Female subject, age 40–49 · the lesion is associated with itching · the lesion involves the head or neck · the patient considered this a rash · the lesion is described as raised or bumpy · the condition has been present for one to four weeks · the photograph is a close-up of the affected area — 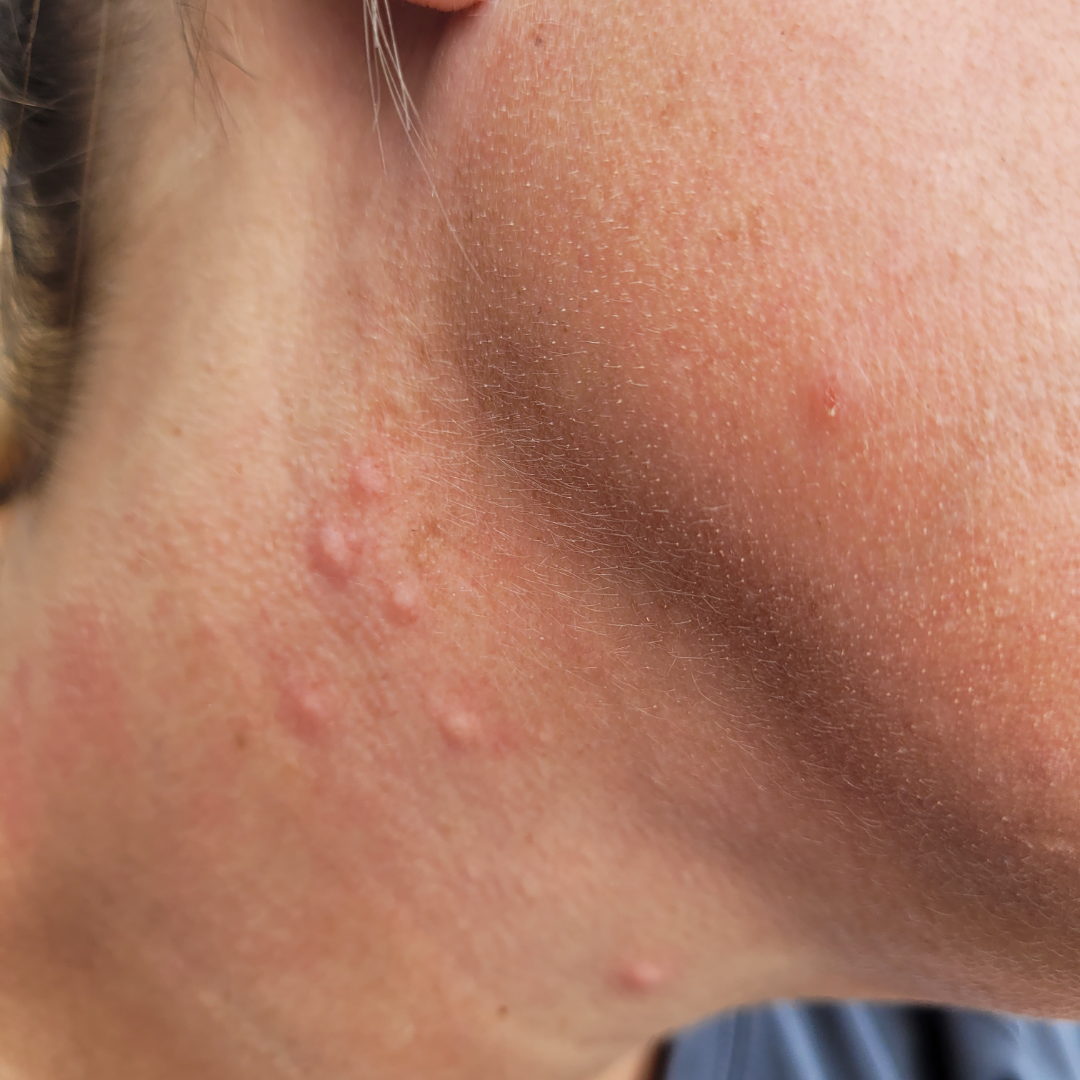Findings:
- assessment · ungradable on photographic review